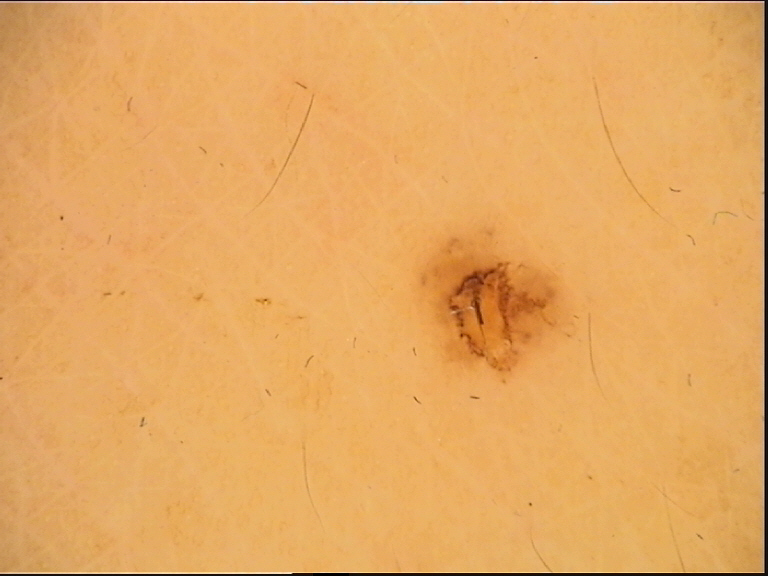Labeled as a benign lesion — a dysplastic compound nevus.